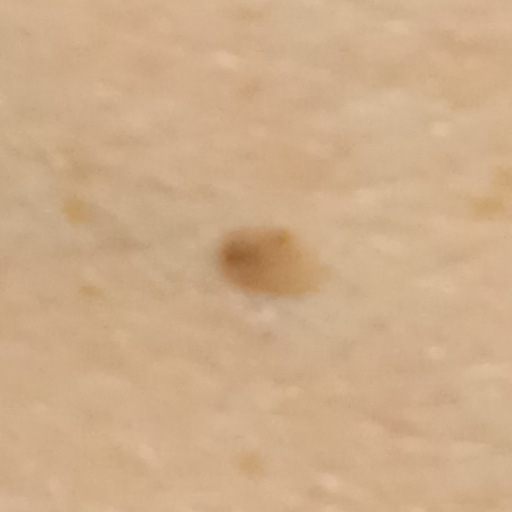| feature | finding |
|---|---|
| sun reaction | skin tans without first burning |
| patient | female, 84 years old |
| referral | research study (no referral diagnosis) |
| risk factors | a personal history of cancer |
| image type | clinical photo |
| location | the torso |
| lesion size | 4.4 mm |
| assessment | seborrheic keratosis (dermatologist consensus) |